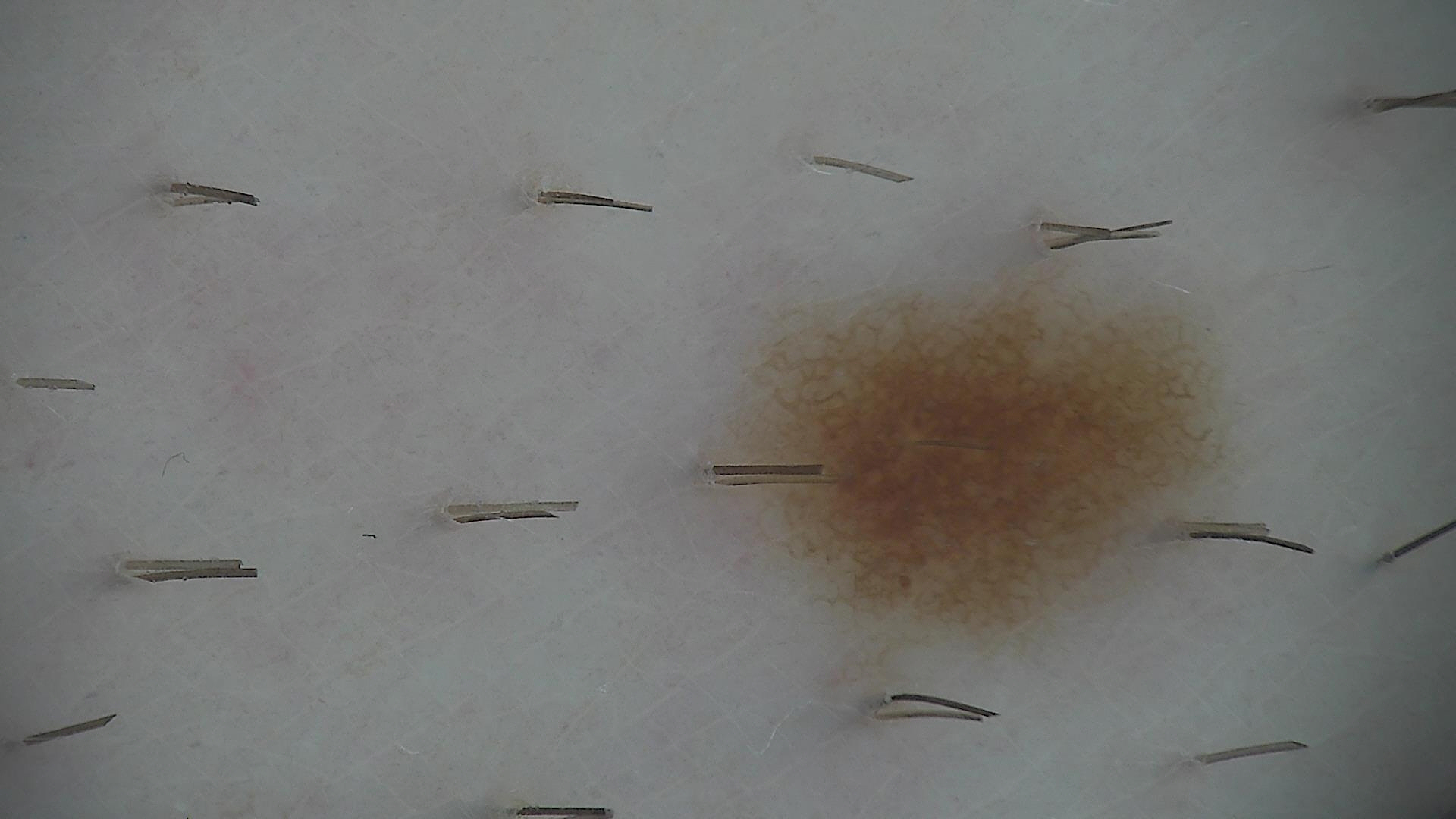A dermoscopic photograph of a skin lesion.
Labeled as a dysplastic junctional nevus.